A dermoscopic image of a skin lesion — 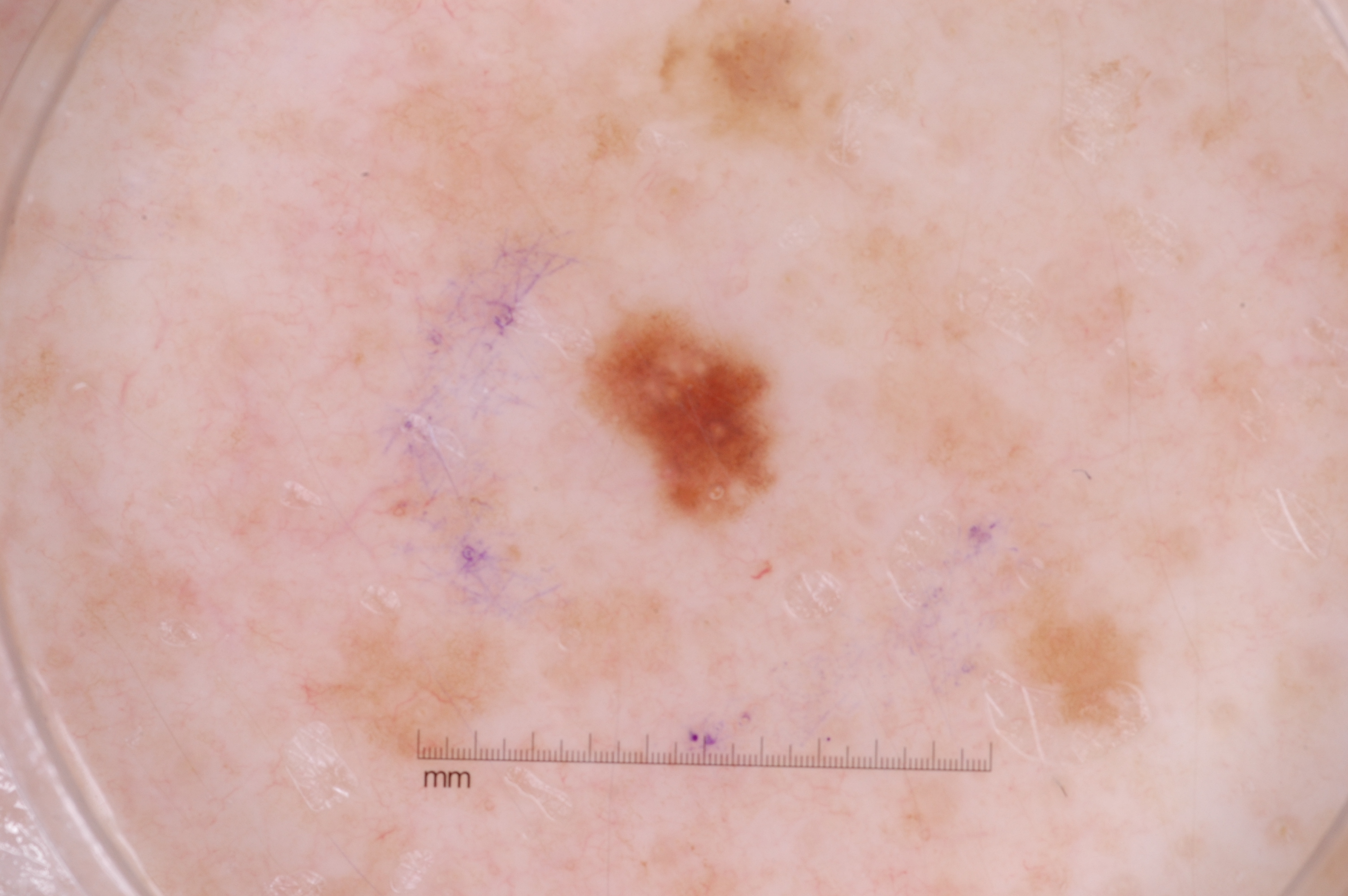location=(577, 294, 785, 542)
dermoscopic pattern=pigment network; absent: negative network, streaks, and milia-like cysts
size=small
assessment=a melanocytic nevus